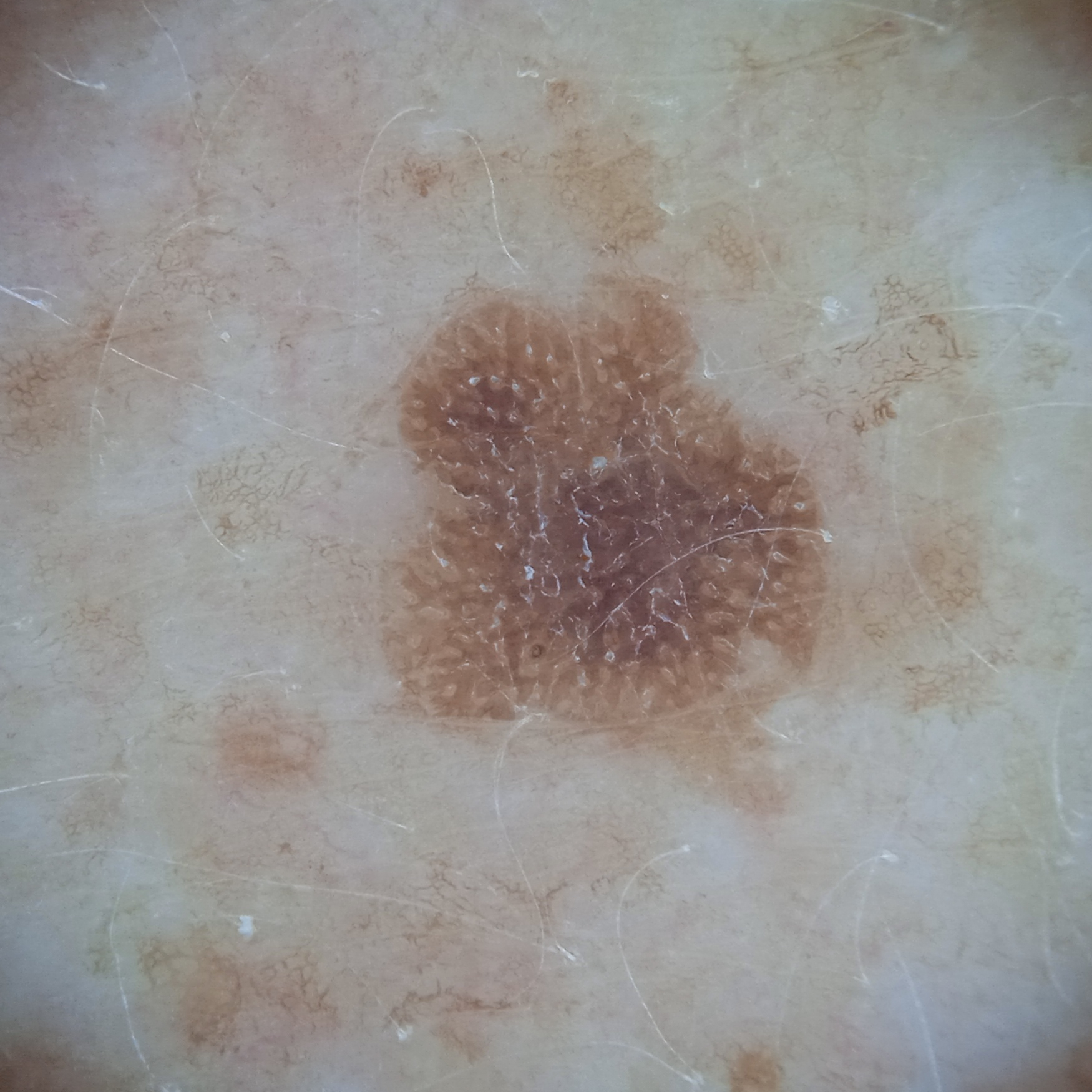<record>
  <image>dermatoscopic image</image>
  <referral>research study (no referral diagnosis)</referral>
  <patient>
    <age>78</age>
    <sex>female</sex>
  </patient>
  <lesion_location>the back</lesion_location>
  <lesion_size>
    <diameter_mm>5.6</diameter_mm>
  </lesion_size>
  <diagnosis>
    <name>seborrheic keratosis</name>
    <malignancy>benign</malignancy>
  </diagnosis>
</record>